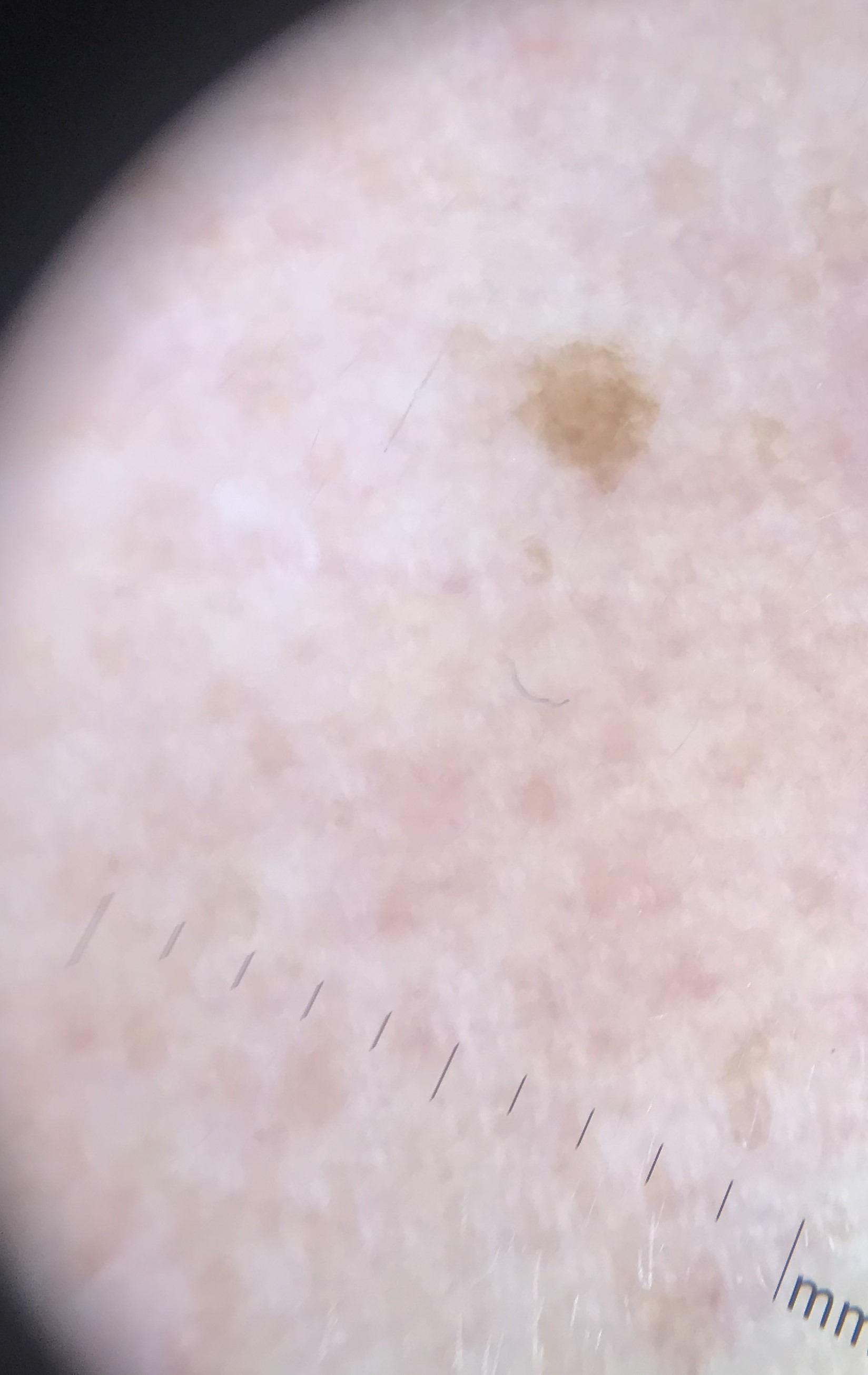Q: What is the lesion category?
A: keratinocytic
Q: What is the diagnosis?
A: seborrheic keratosis (expert consensus)